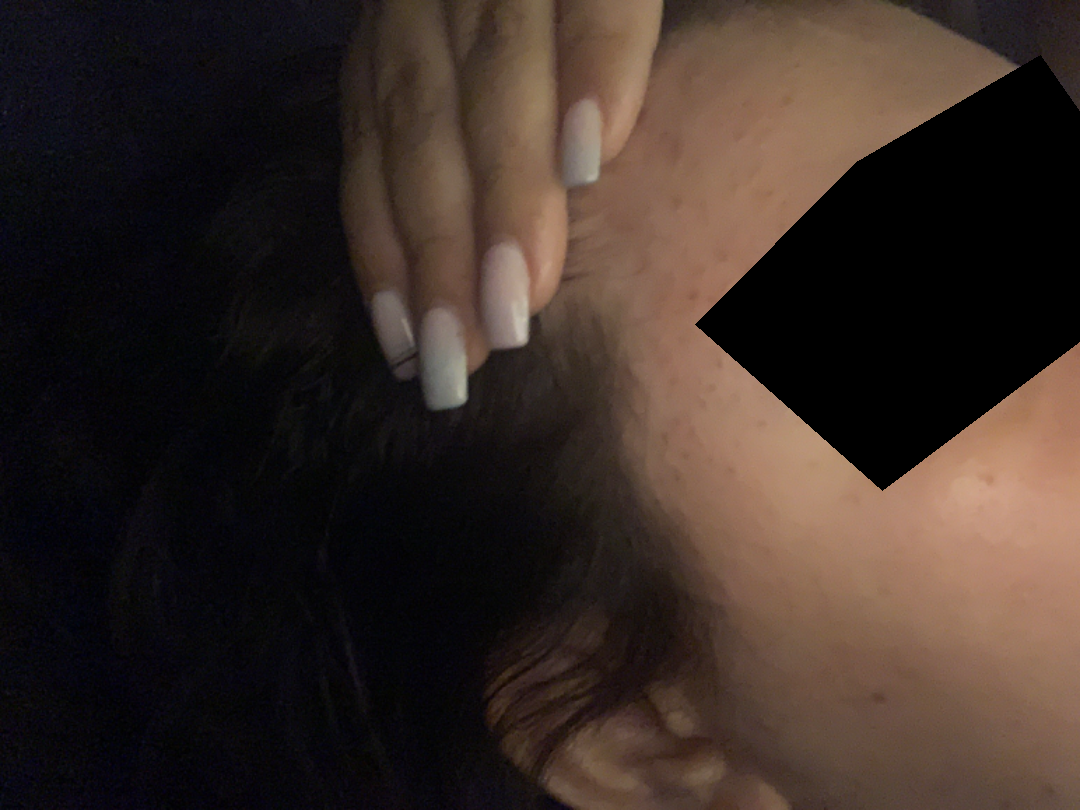Assessment: The skin findings could not be characterized from the image.